The subject is a male aged approximately 80, a dermoscopic image of a skin lesion:
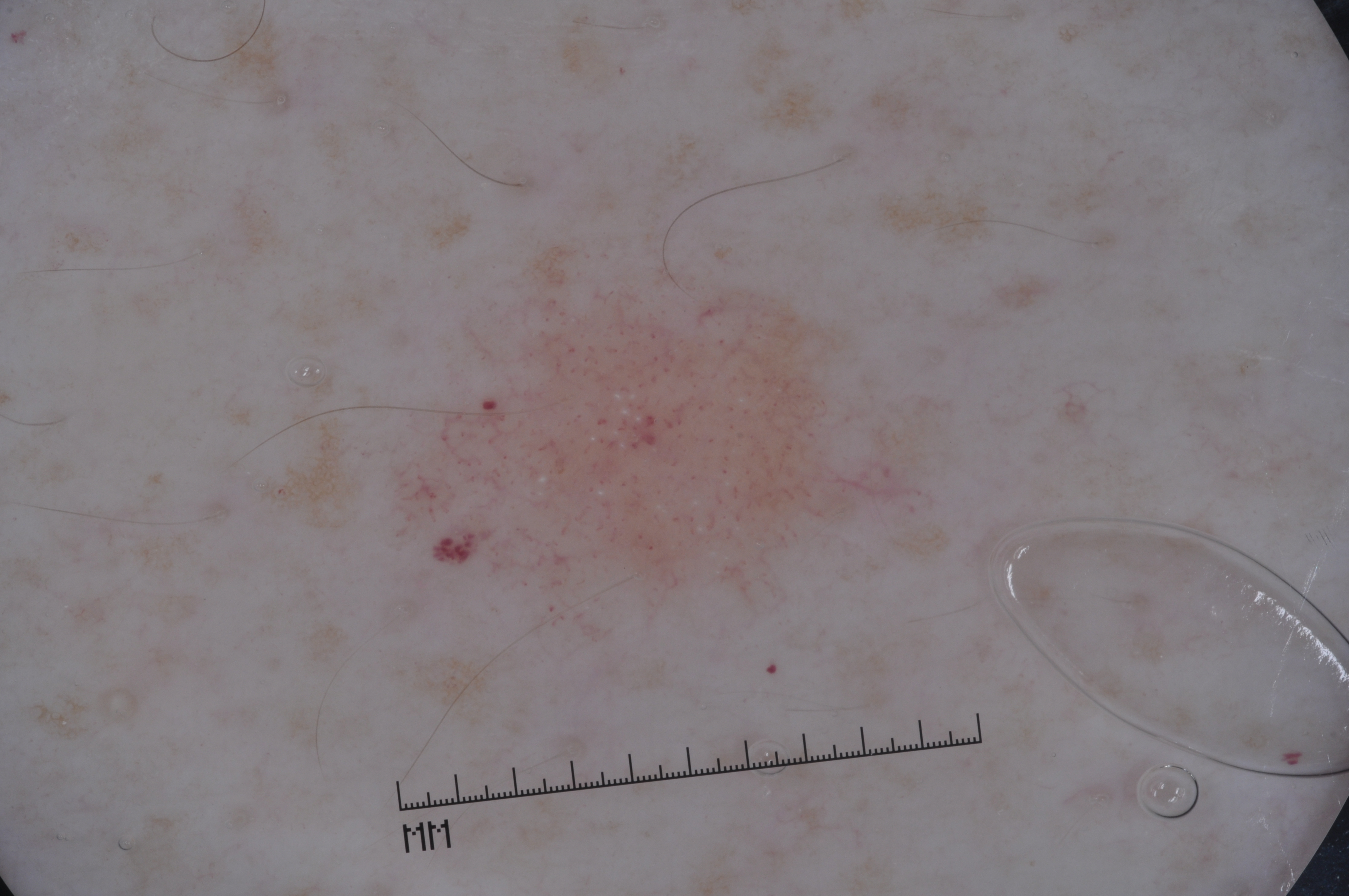Case summary:
A moderately sized lesion. Dermoscopic examination shows milia-like cysts; no pigment network, negative network, or streaks. The visible lesion spans x1=390 y1=241 x2=933 y2=627.
Assessment:
Expert review diagnosed this as a melanocytic nevus, a benign lesion.